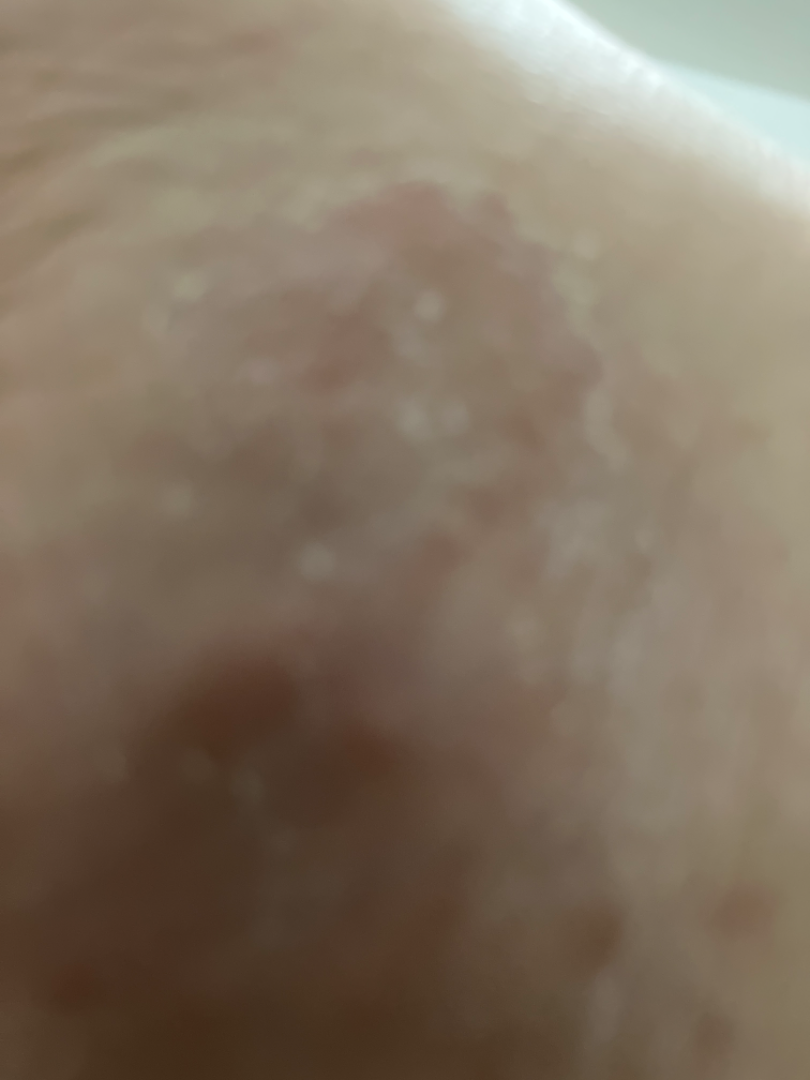assessment — indeterminate from the photograph
contributor — female, age 18–29
patient describes the issue as — a rash
view — close-up
lesion symptoms — bothersome appearance, itching and burning
location — top or side of the foot
surface texture — raised or bumpy and rough or flaky
duration — more than one year
skin tone — self-reported FST I